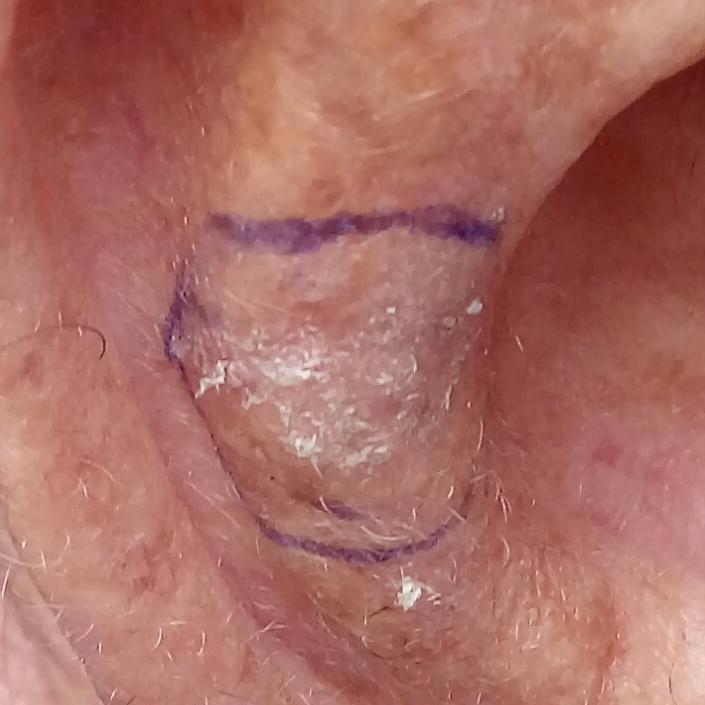Case summary: A subject in their 60s. A clinical photo of a skin lesion taken with a smartphone. The lesion is on an ear. Per patient report, the lesion itches, but does not hurt and has not changed. Conclusion: The clinical impression was an actinic keratosis.